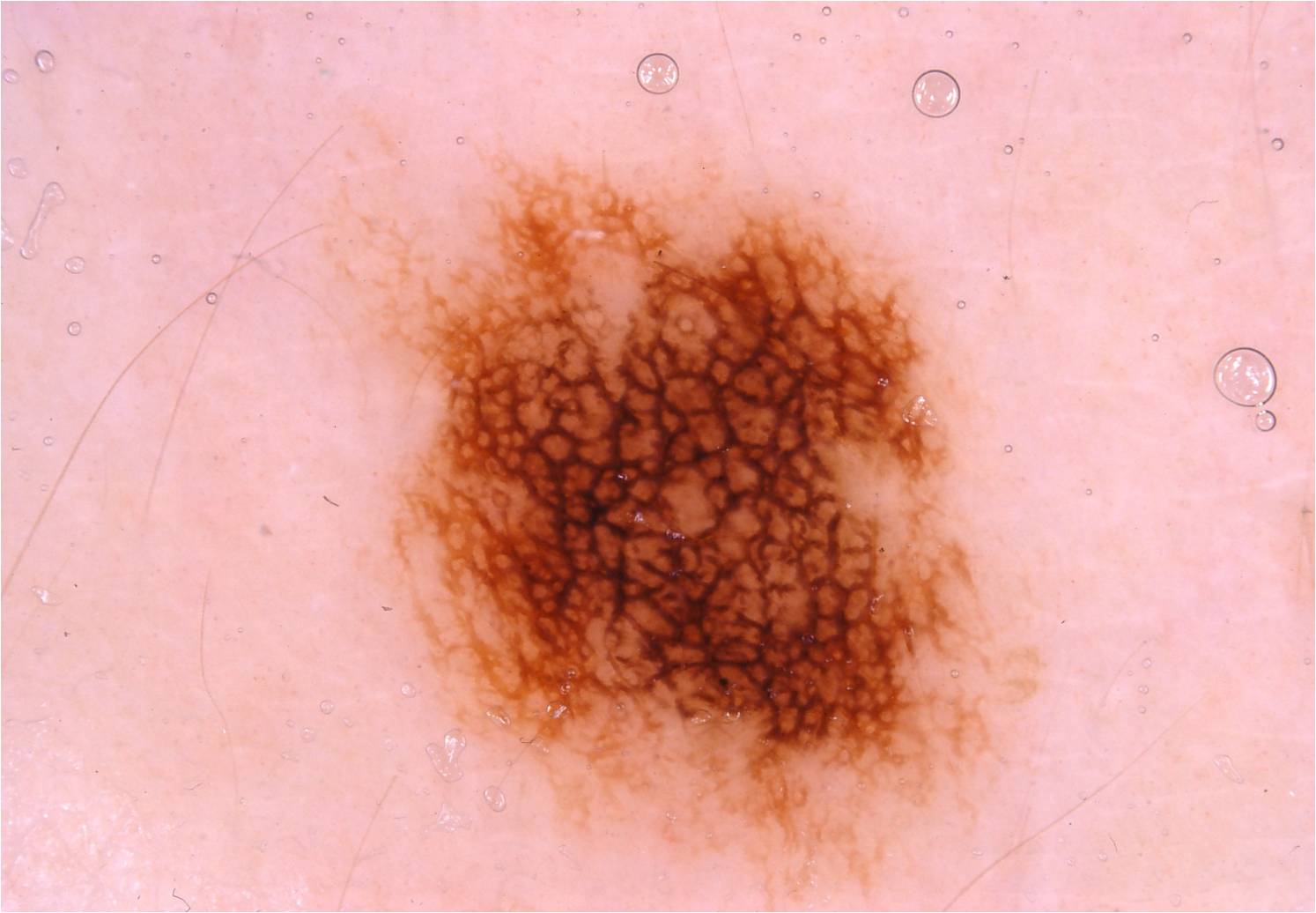- imaging — dermoscopic image
- patient — female, aged approximately 10
- size — large
- bounding box — <bbox>322, 149, 1041, 898</bbox>
- dermoscopic findings — pigment network; absent: streaks, negative network, milia-like cysts, and globules
- assessment — a melanocytic nevus, a benign lesion